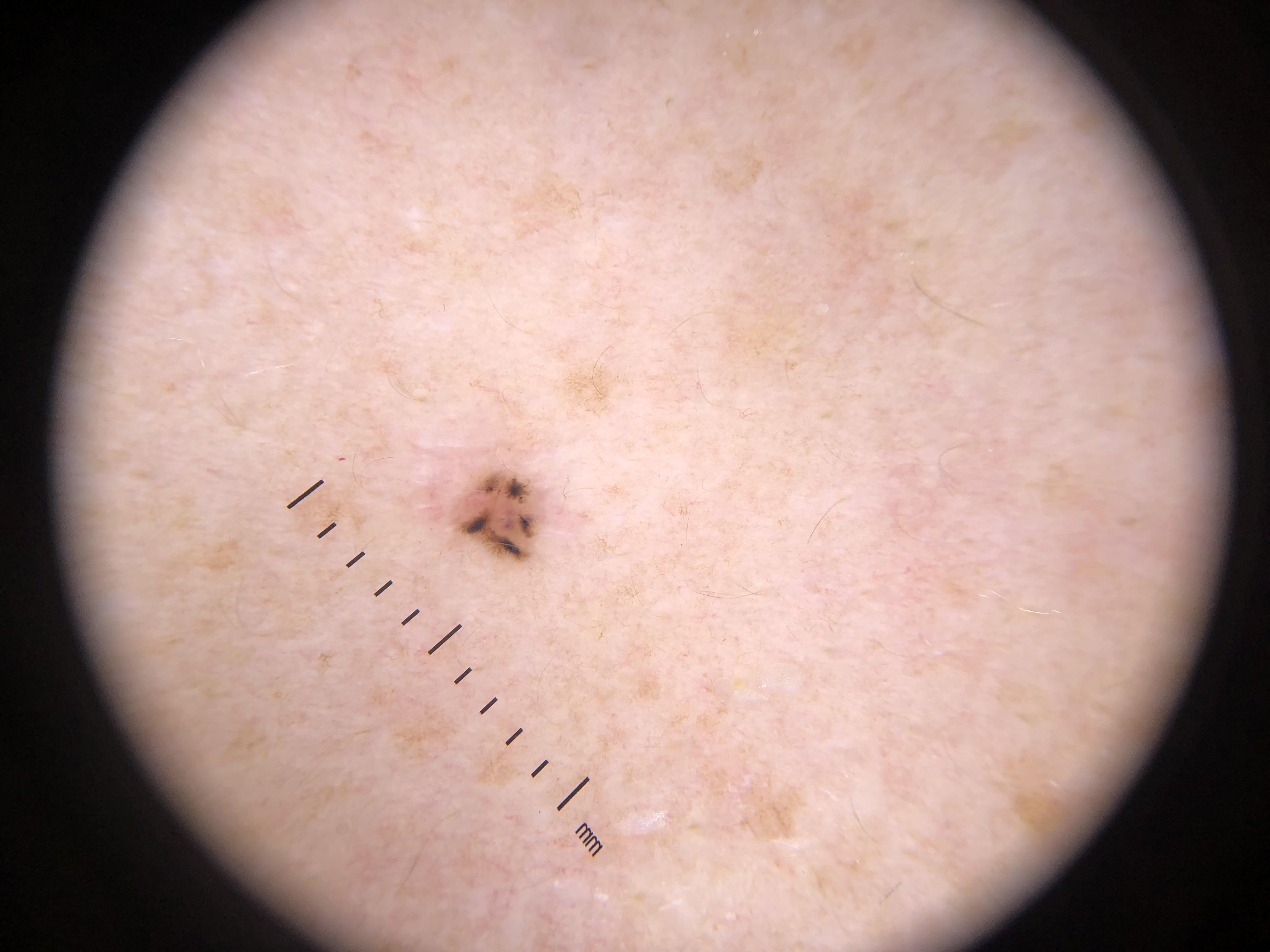{
  "image": "dermatoscopic image",
  "lesion_location": {
    "region": "the trunk",
    "detail": "the anterior trunk"
  },
  "diagnosis": {
    "name": "Basal cell carcinoma",
    "malignancy": "malignant",
    "confirmation": "histopathology",
    "lineage": "adnexal"
  }
}